The front of the torso, leg, top or side of the foot and back of the torso are involved · the subject is female · close-up view:
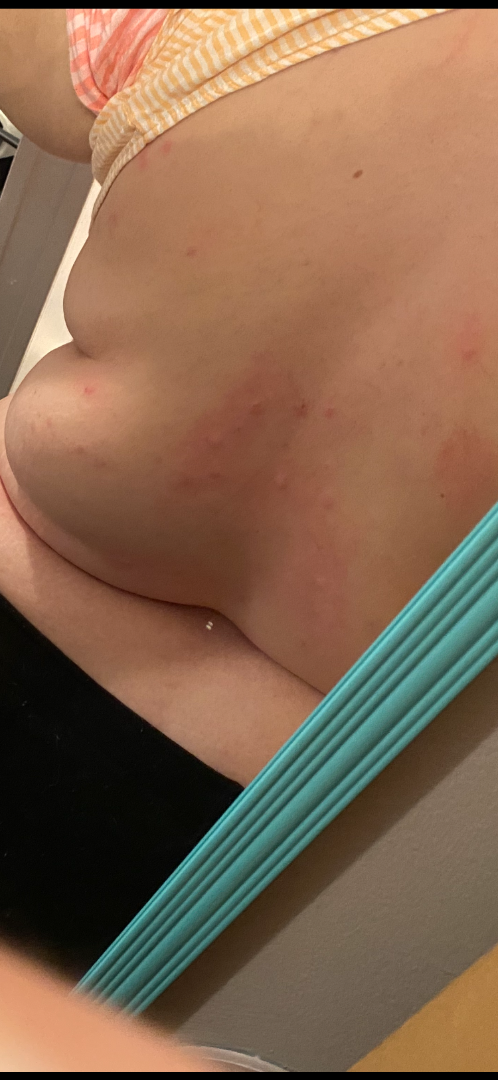The skin findings could not be characterized from the image.
The contributor notes the lesion is fluid-filled and raised or bumpy.
Reported duration is one to four weeks.
The lesion is associated with itching and burning.
The patient considered this a rash.